A dermoscopic close-up of a skin lesion.
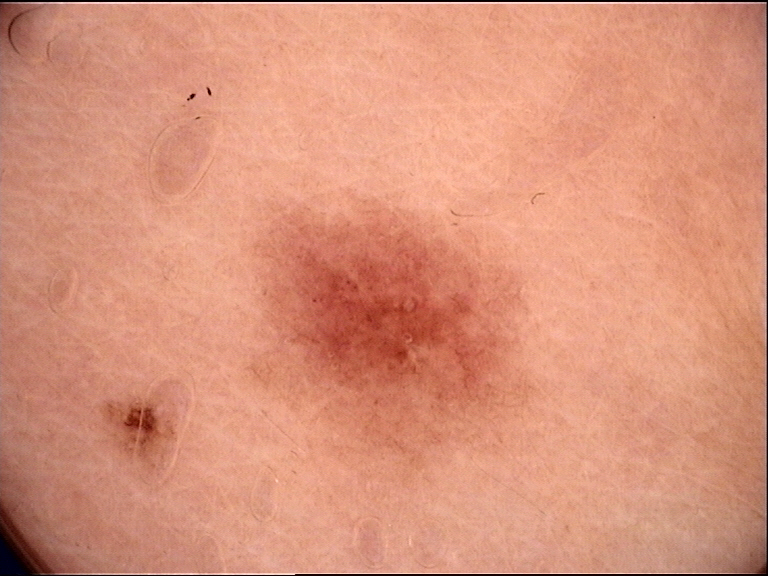The diagnosis was a benign lesion — a dysplastic junctional nevus.